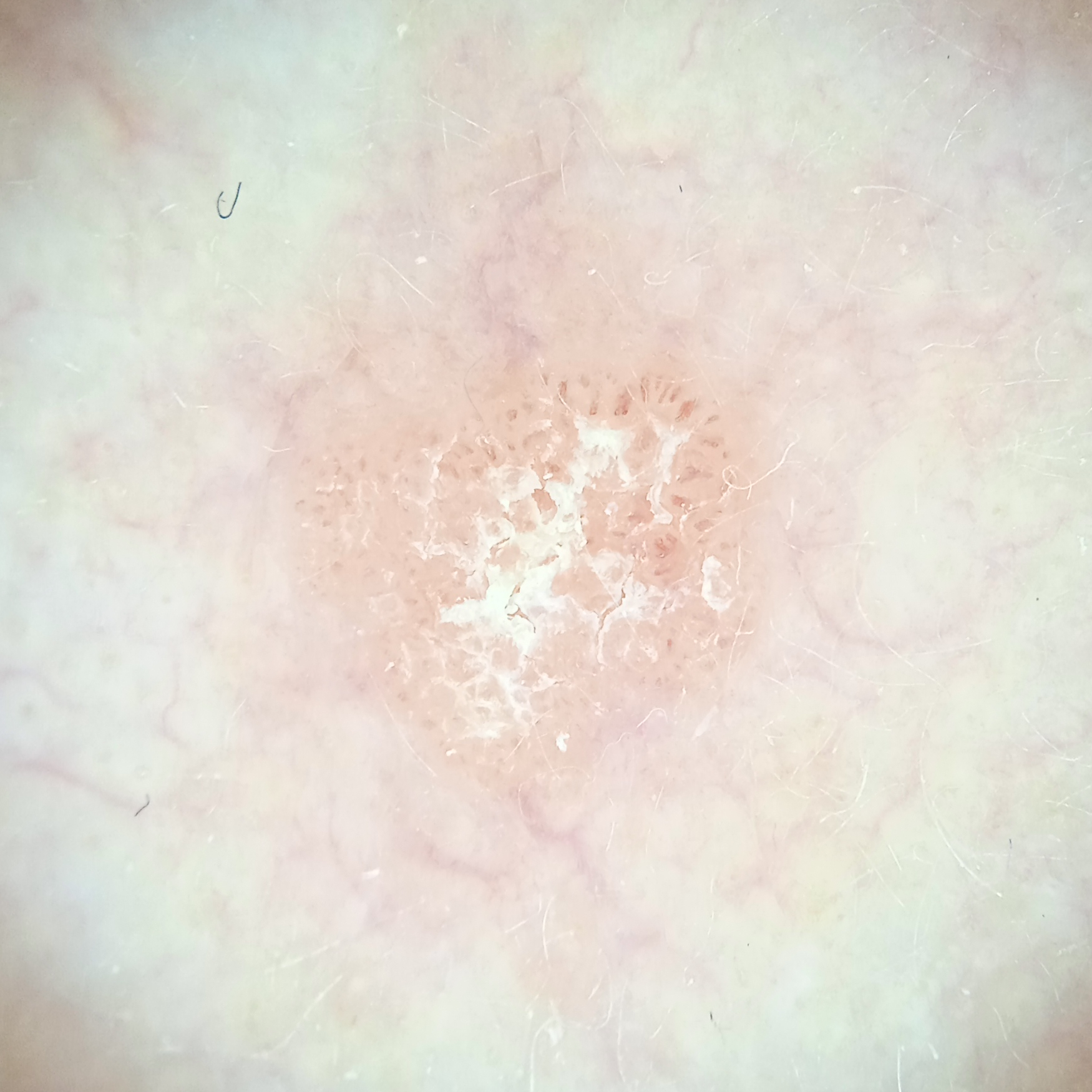The patient says their skin reddens with sun exposure.
Acquired for a research image collection, with no referral diagnosis.
A dermoscopy image of a skin lesion.
By self-report, a personal history of cancer and a personal history of skin cancer.
A male subject 77 years old.
The patient describes having a moderate number of moles.
The lesion is on the face.
Measuring roughly 4.3 mm.
Dermatologist review favored an actinic keratosis.